A dermoscopic photograph of a skin lesion.
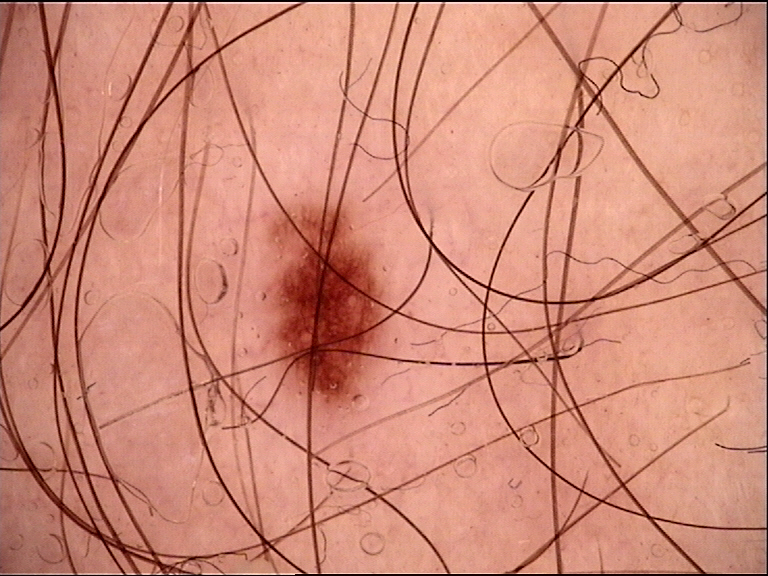The morphology is that of a banal lesion. Classified as a junctional nevus.